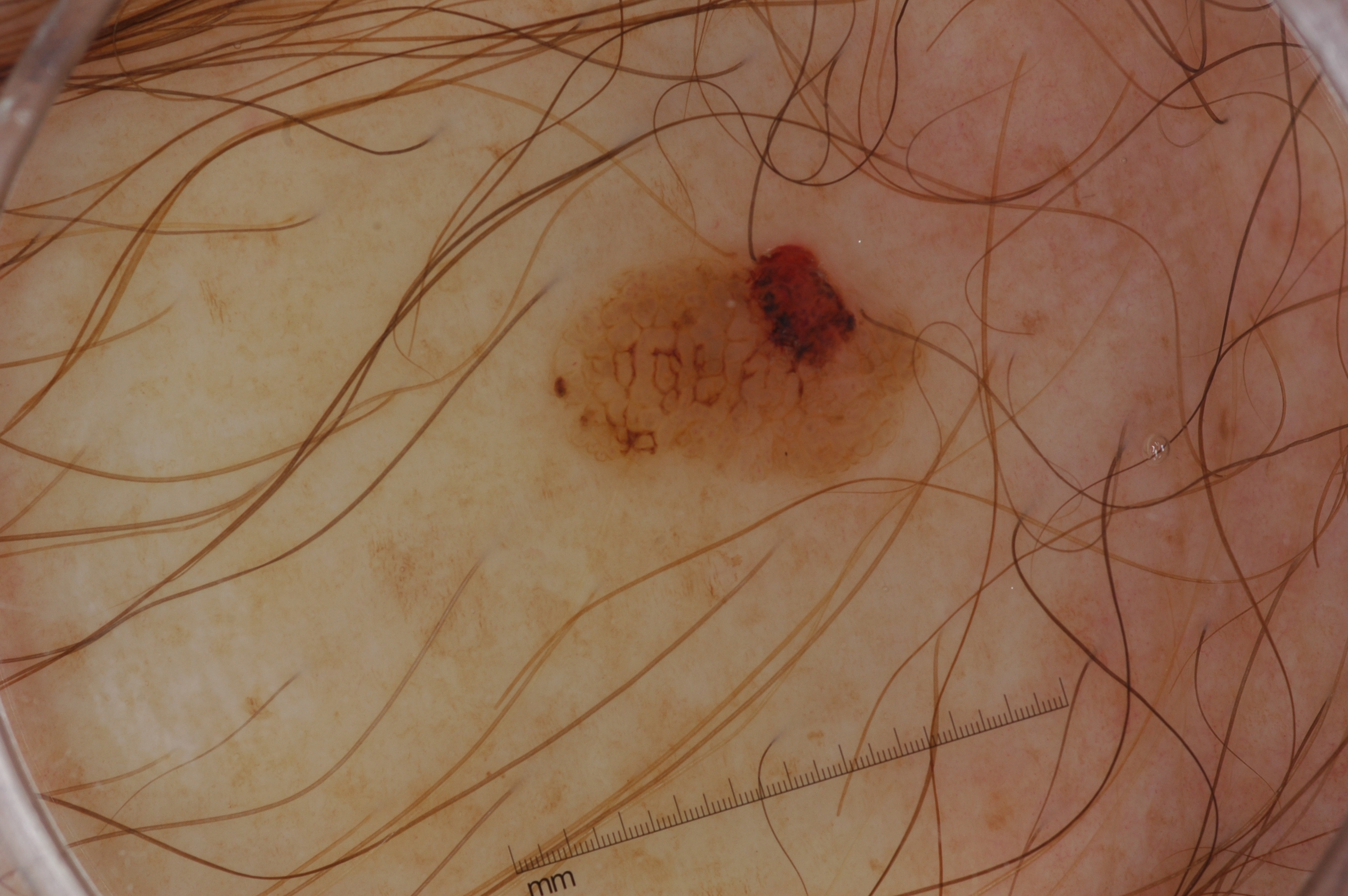A male subject in their mid- to late 40s. Dermoscopy of a skin lesion. The visible lesion spans (558, 238, 916, 476). Dermoscopic assessment notes no milia-like cysts, streaks, pigment network, or negative network. The diagnostic assessment was a seborrheic keratosis, a benign skin lesion.